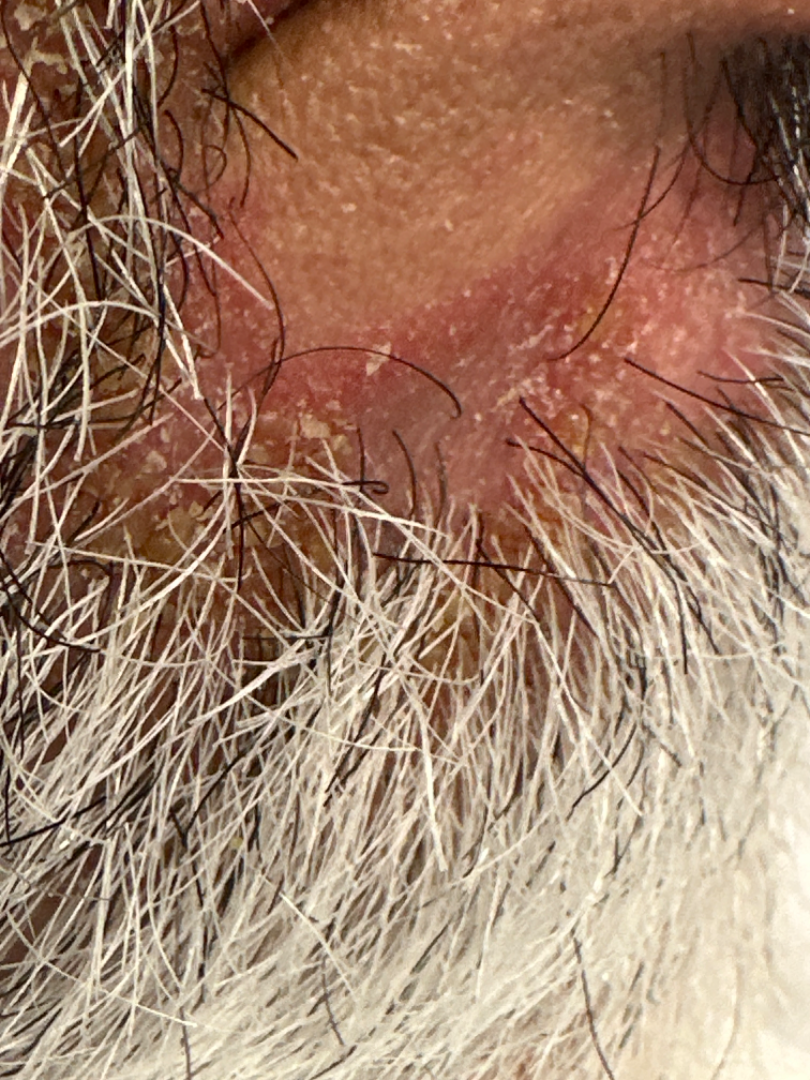Patient information: The photograph was taken at an angle. Review: Reviewed remotely by one dermatologist: consistent with Seborrheic Dermatitis.